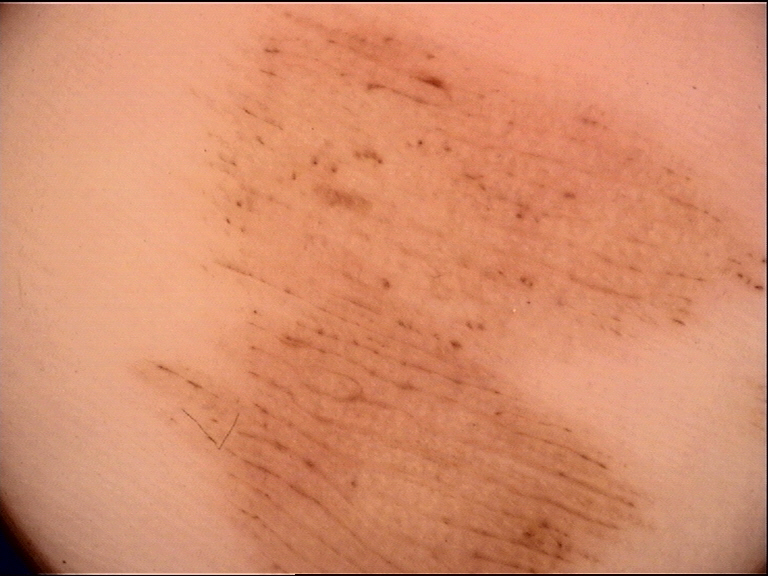Labeled as an acral junctional nevus.